This is a close-up image:
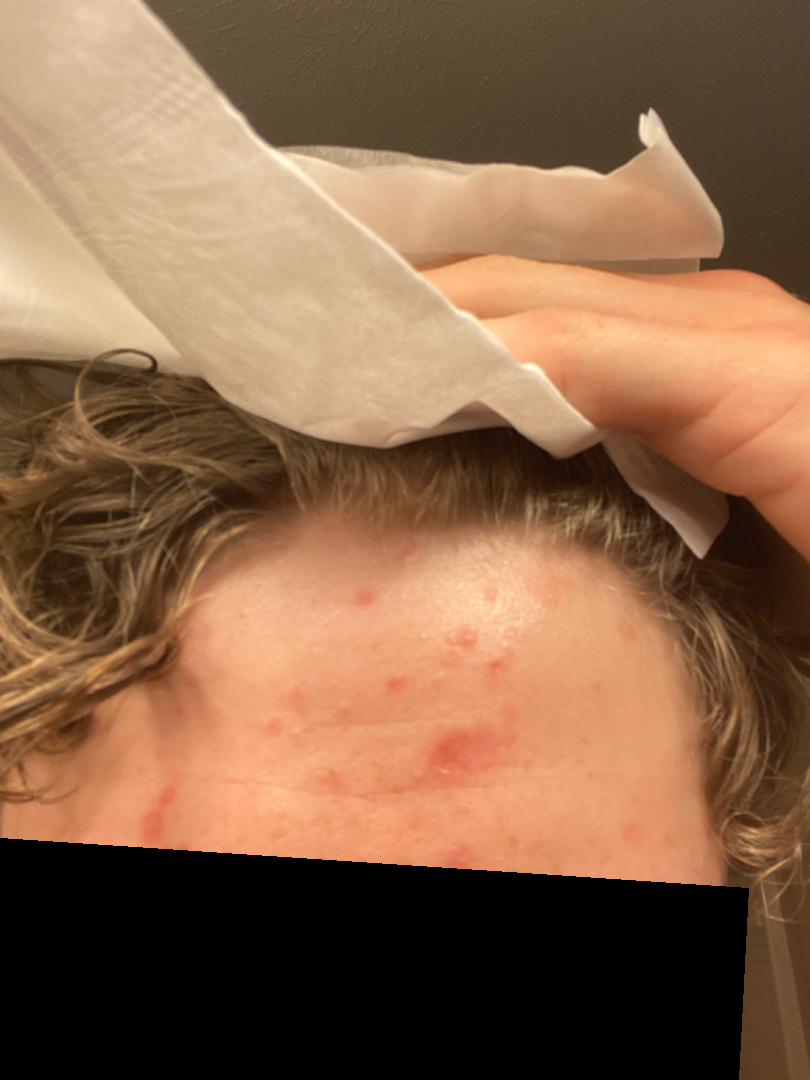The skin findings could not be characterized from the image.